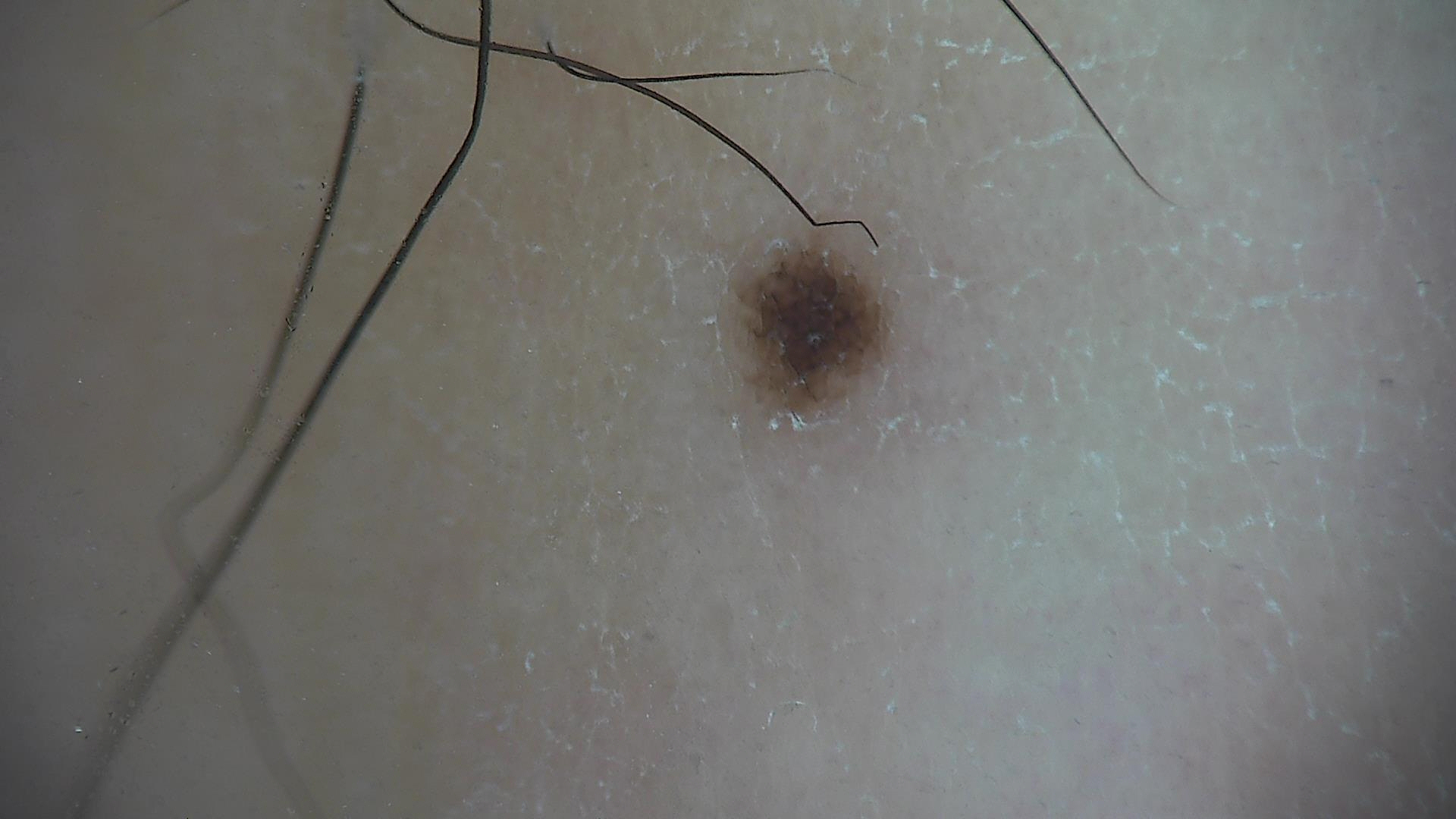A skin lesion imaged with a dermatoscope.
Consistent with a benign lesion — a dysplastic junctional nevus.